Close-up view: 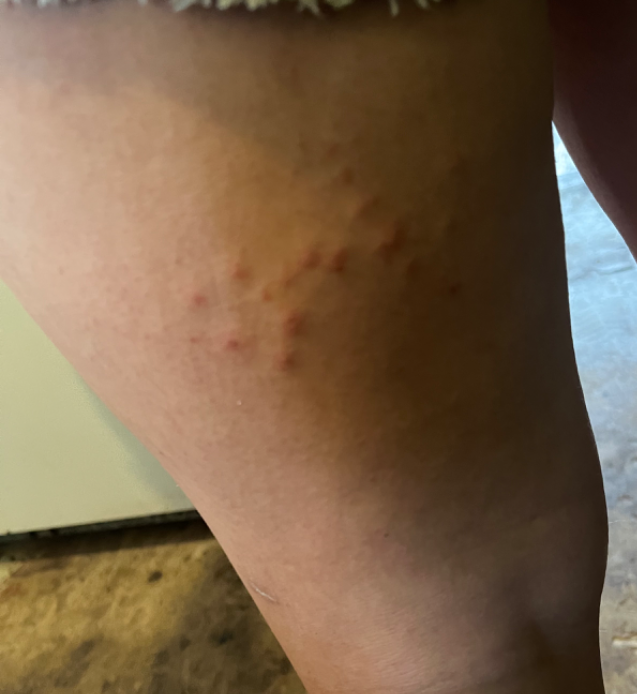Diagnostic features were not clearly distinguishable in this photograph.